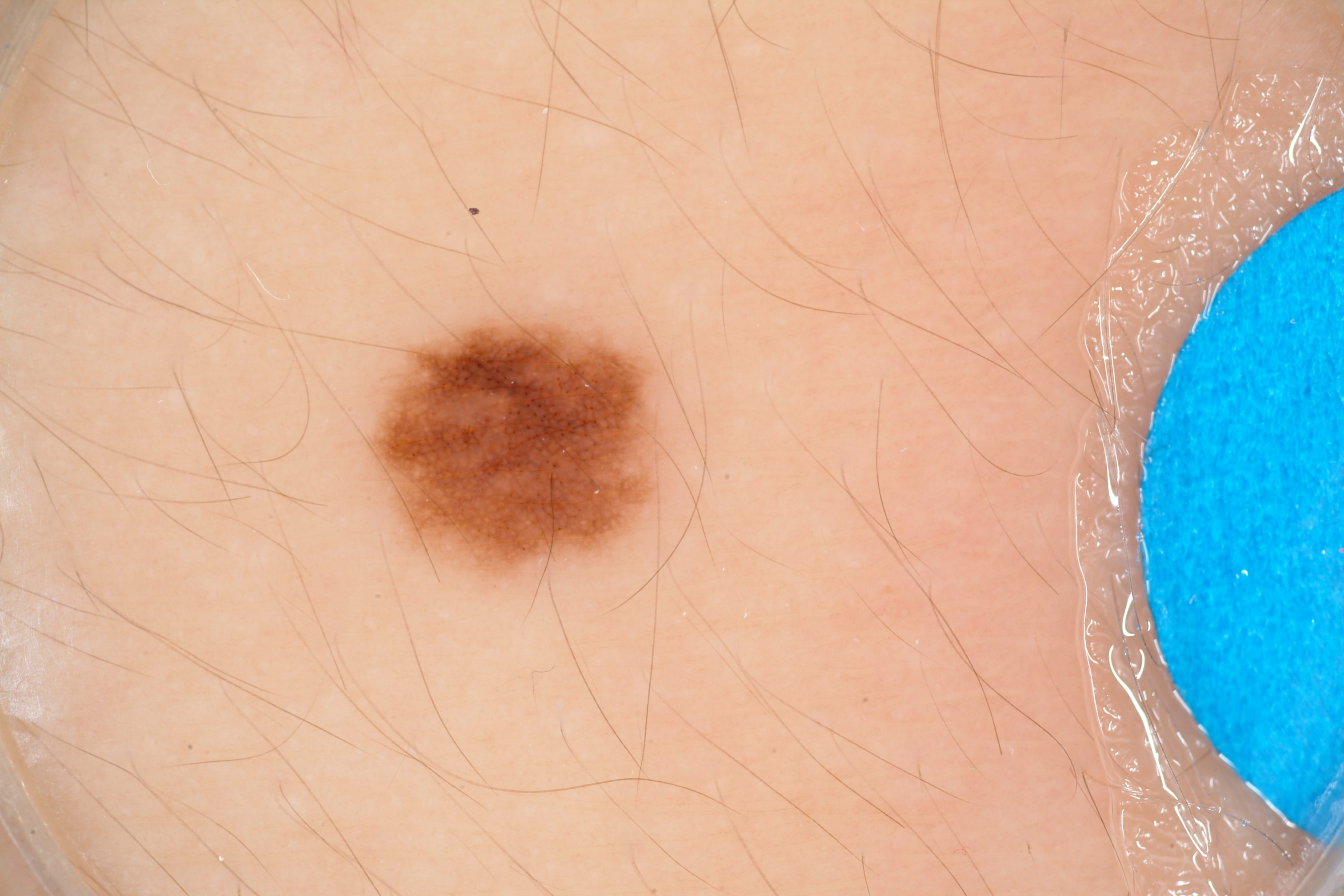Dermoscopy of a skin lesion.
Dermoscopic assessment notes pigment network.
With coordinates (x1, y1, x2, y2), the lesion is located at bbox=[362, 301, 689, 593].
The clinical diagnosis was a melanocytic nevus.